The affected area is the arm and leg · the patient is a male aged 50–59 · this is a close-up image:
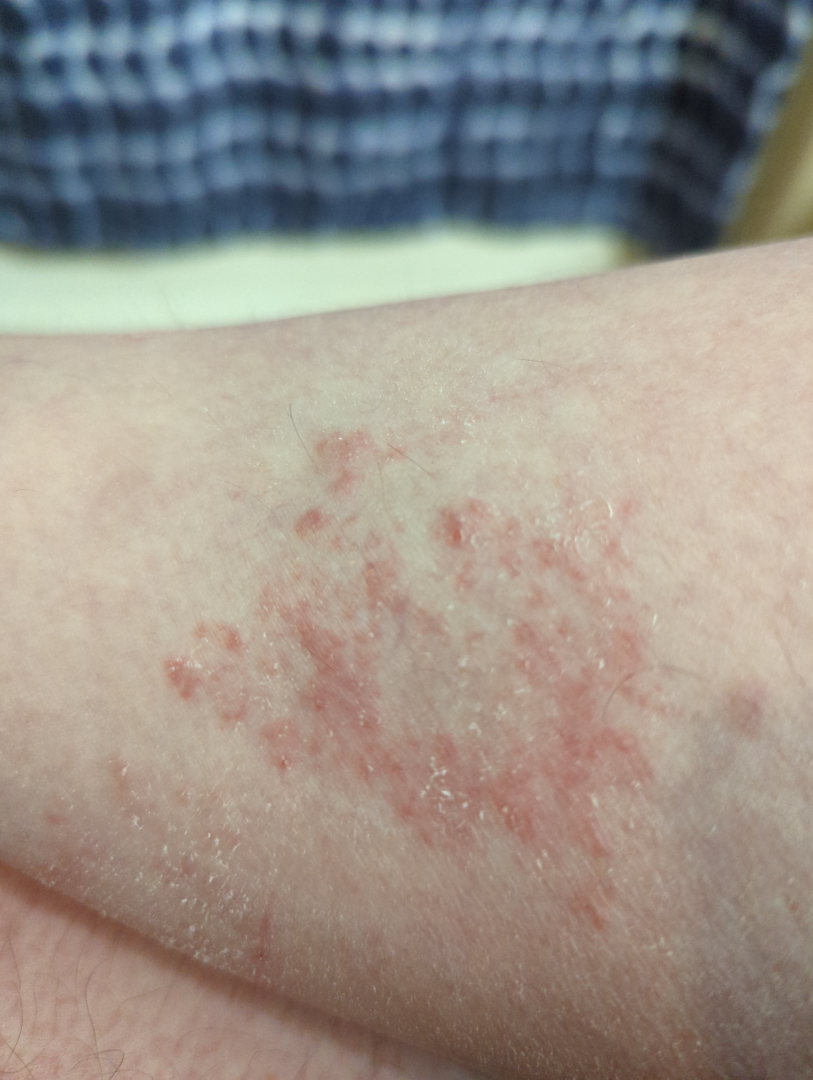differential = three dermatologists each reviewed the case: favoring Eczema; with consideration of Allergic Contact Dermatitis; also raised was Acute dermatitis, NOS; less likely is Tinea; less probable is Stasis Dermatitis.